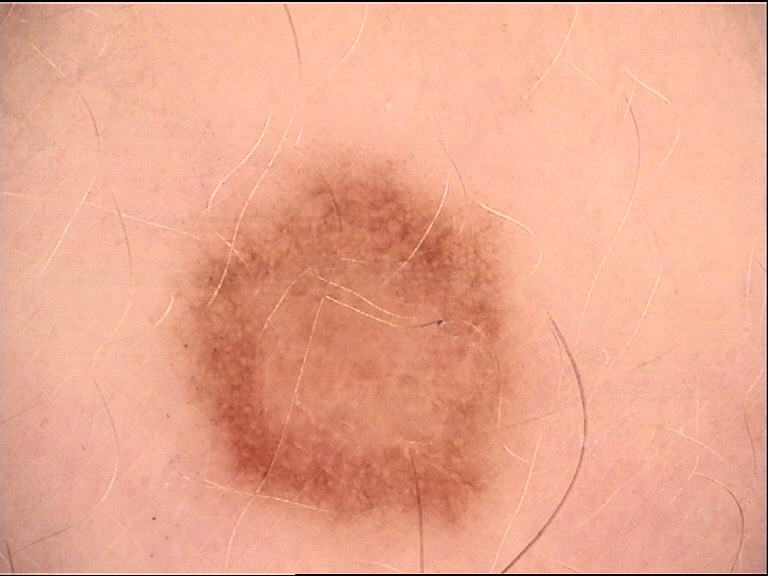Case:
* class — dysplastic junctional nevus (expert consensus)